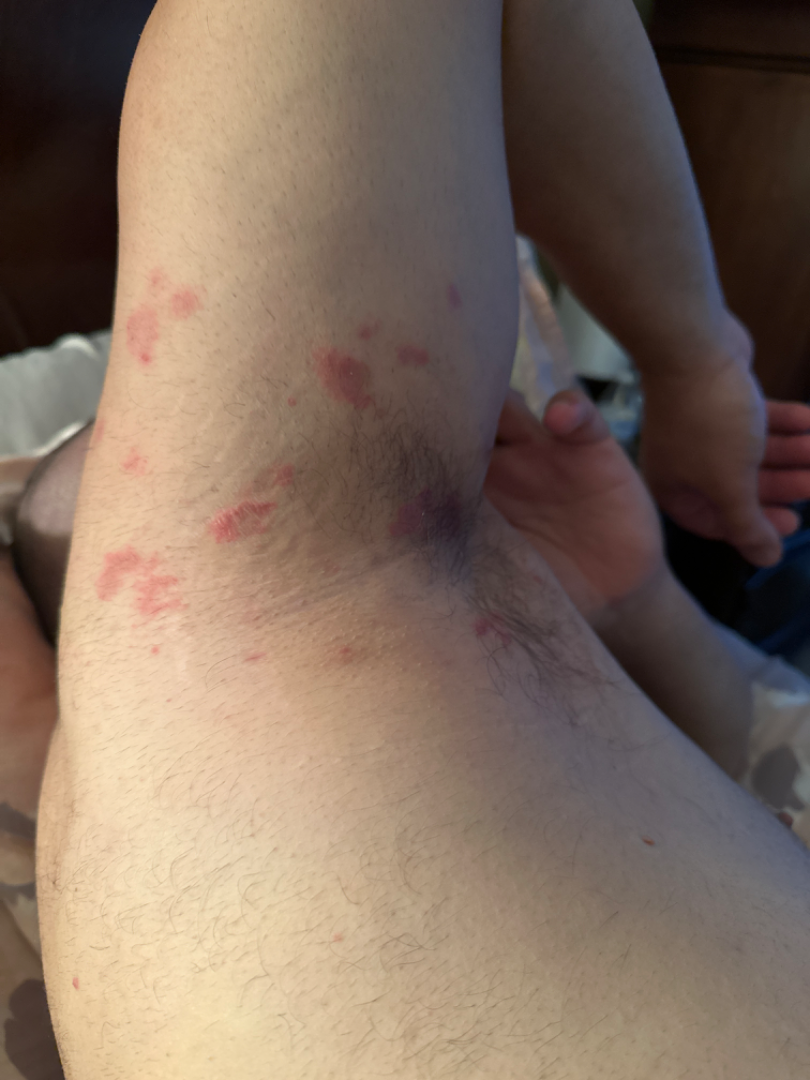History: The contributor is a male aged 40–49. Reported lesion symptoms include itching, darkening, enlargement, burning and bothersome appearance. This image was taken at an angle. Located on the arm. The condition has been present for one to three months. Impression: On photographic review by a dermatologist: Eczema (67%); Psoriasis (33%).